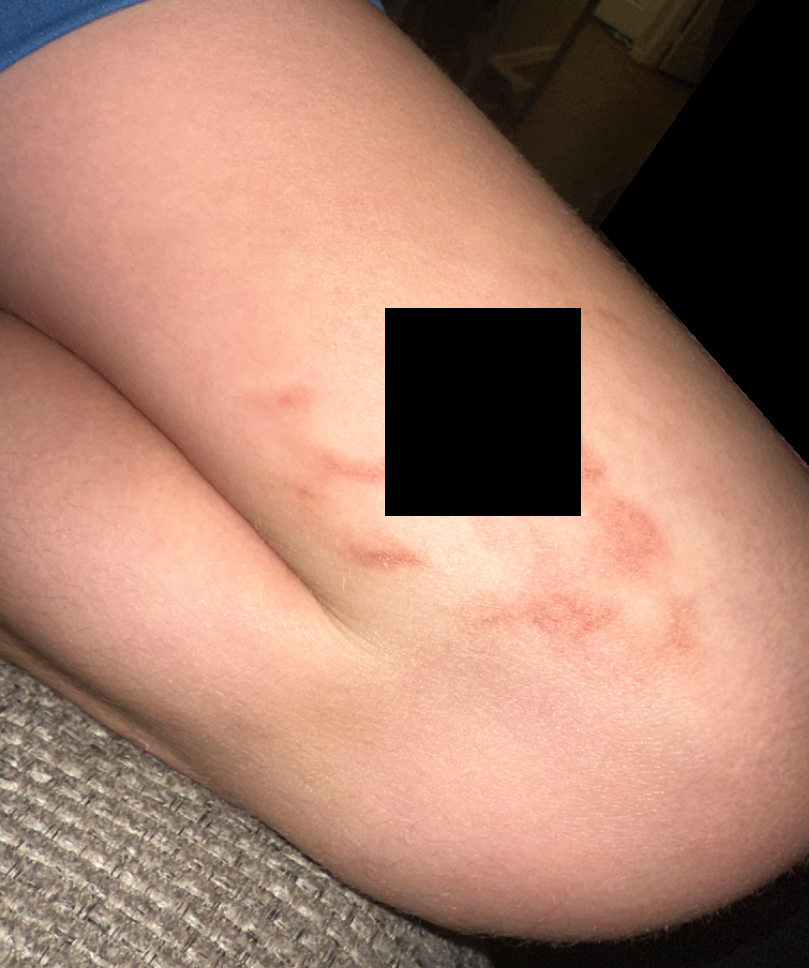Review: The skin findings could not be characterized from the image. Patient information: Close-up view. The patient reported no systemic symptoms. Self-categorized by the patient as a rash. The leg is involved. Present for one to three months. The patient notes bothersome appearance.